This is a close-up image. The patient is 40–49, female — 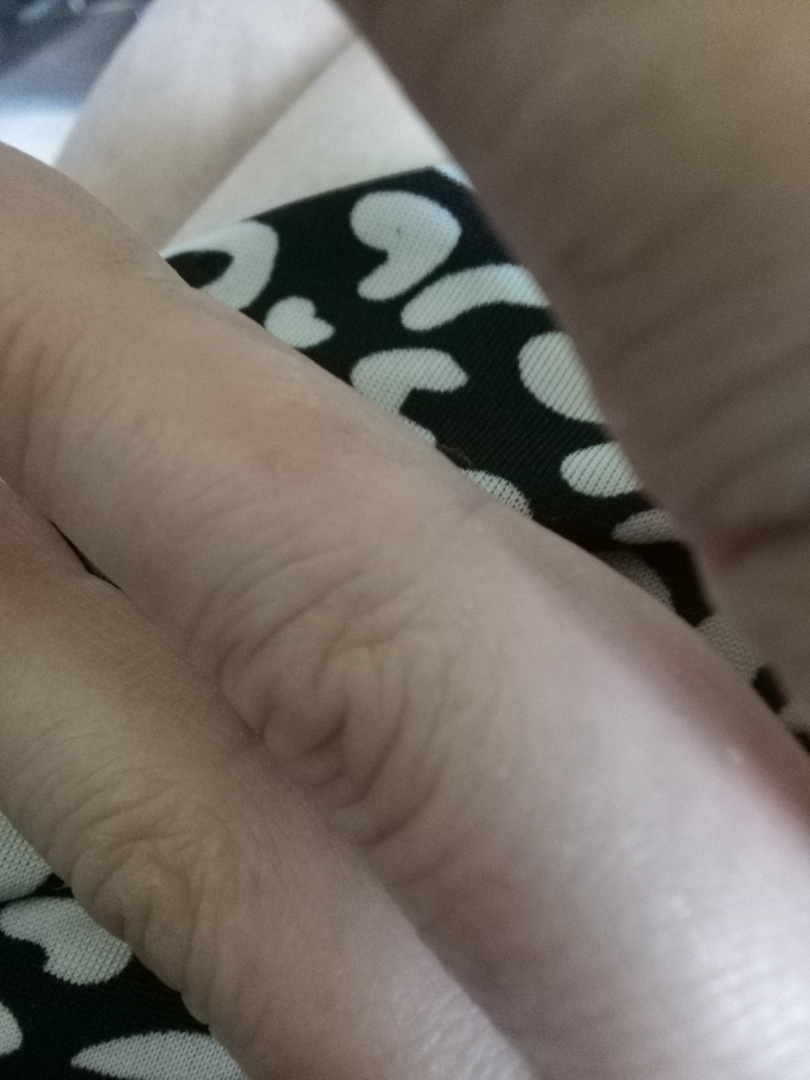differential diagnosis = the primary impression is Eczema; with consideration of Scabies.